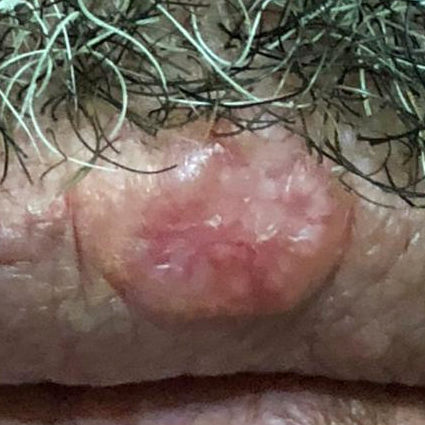History notes prior skin cancer (patient or family). A male subject age 58. The patient is Fitzpatrick phototype IV. A clinical photograph showing a skin lesion. The lesion measures approximately 11 × 10 mm. Per patient report, the lesion has grown and is elevated. Biopsy-confirmed as a basal cell carcinoma.